An image taken at an angle. The leg is involved:
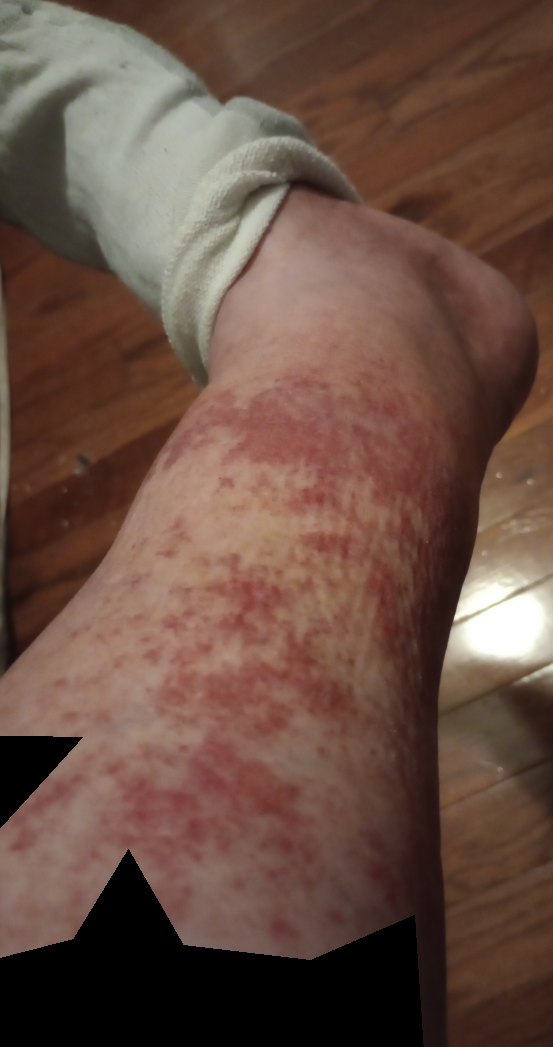The skin condition could not be confidently assessed from this image. The patient described the issue as a rash. The lesion is associated with bothersome appearance, enlargement, burning and pain. Reported duration is less than one week. The lesion is described as raised or bumpy.